The patient says their skin reddens painfully with sun exposure. The patient describes having a moderate number of moles. A female subject aged 50. A clinical photograph of a skin lesion.
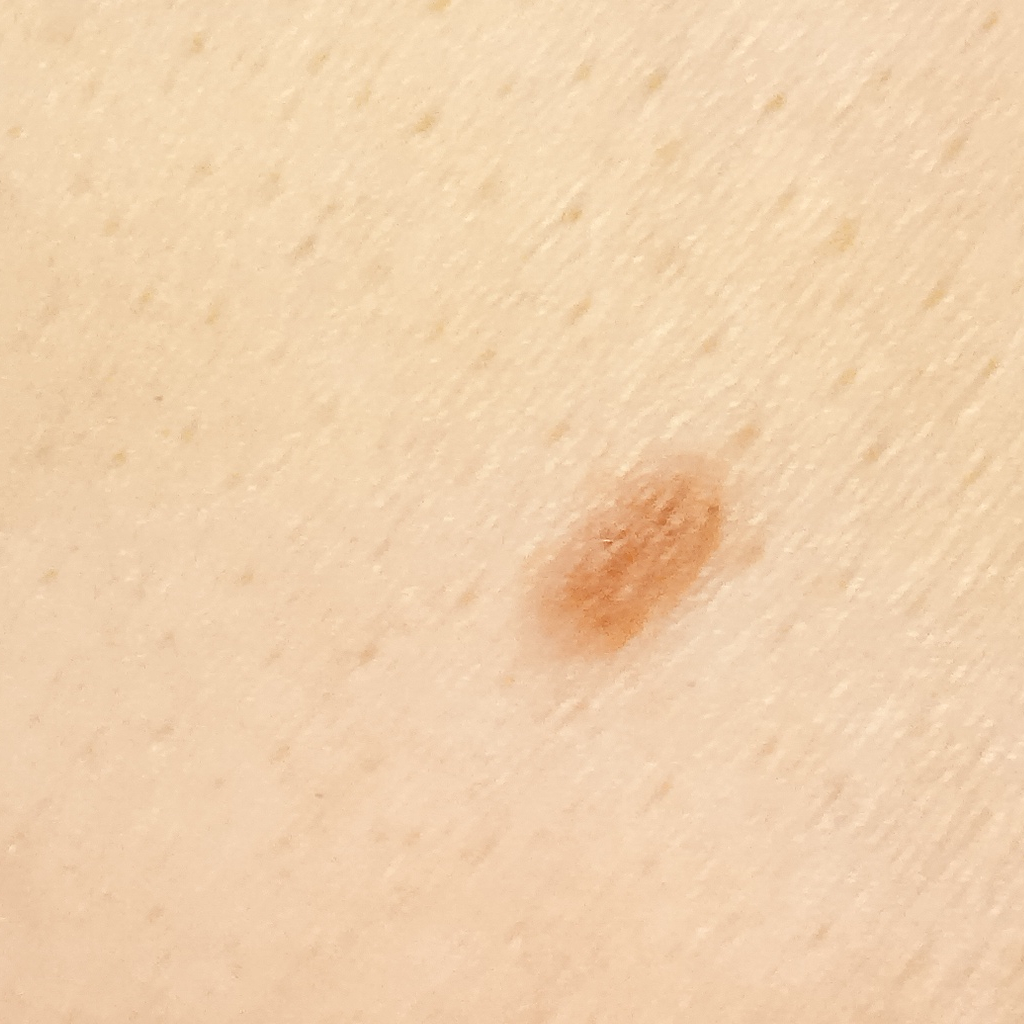The lesion is located on the torso.
Measuring roughly 4.9 mm.
The diagnostic impression was a melanocytic nevus.